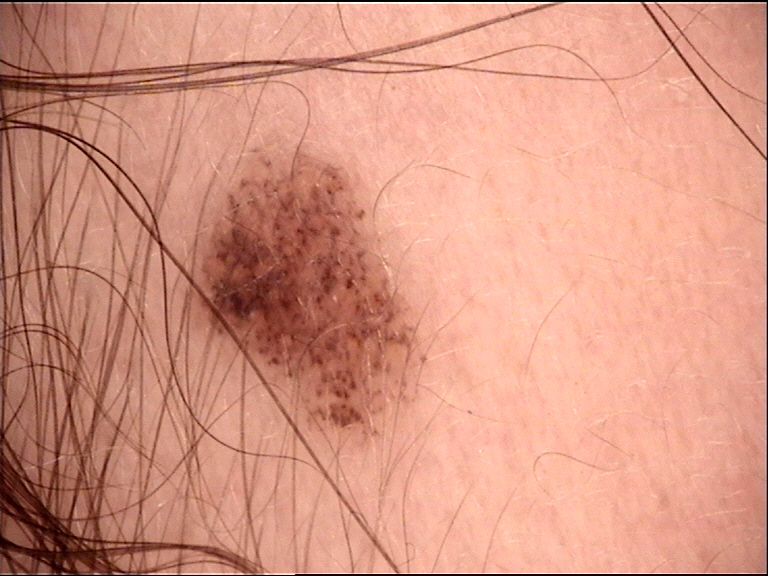Dermoscopy of a skin lesion. The diagnostic label was a dysplastic junctional nevus.